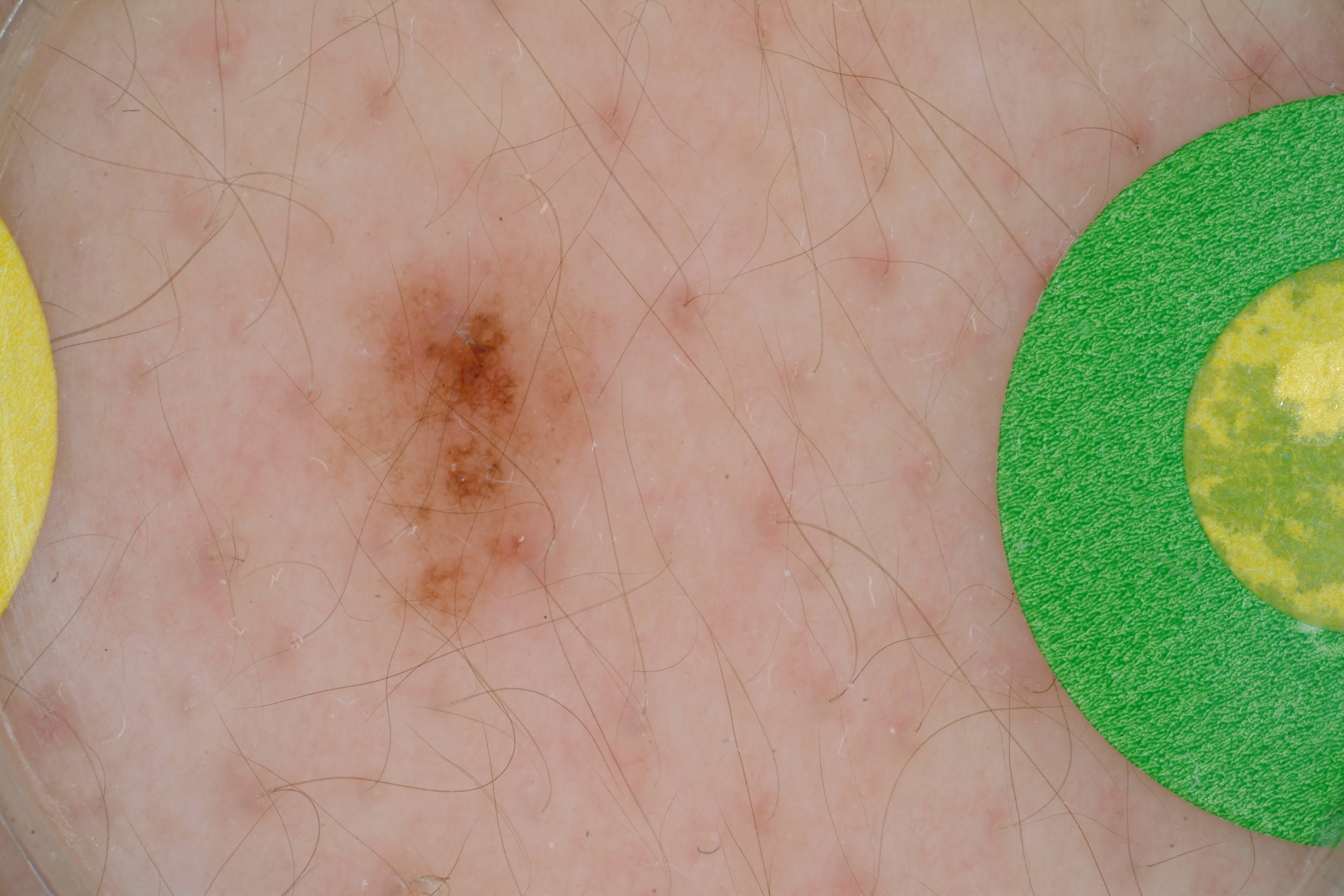A dermoscopic image of a skin lesion.
A male patient, aged around 15.
In (x1, y1, x2, y2) order, the lesion is located at bbox=[321, 221, 617, 650].
The dermoscopic pattern shows globules and pigment network, with no streaks, negative network, or milia-like cysts.
Consistent with a melanocytic nevus, a benign skin lesion.